The contributor is 50–59, female. The patient indicates the lesion is rough or flaky and raised or bumpy. The lesion involves the leg, arm and back of the hand. The patient considered this a rash. The lesion is associated with pain, bleeding, darkening, enlargement, itching, burning and bothersome appearance. Reported duration is more than one year. Self-reported Fitzpatrick IV; lay reviewers estimated Monk Skin Tone 3 or 4 (two reviewer pools). An image taken at a distance. Associated systemic symptoms include joint pain and fatigue — 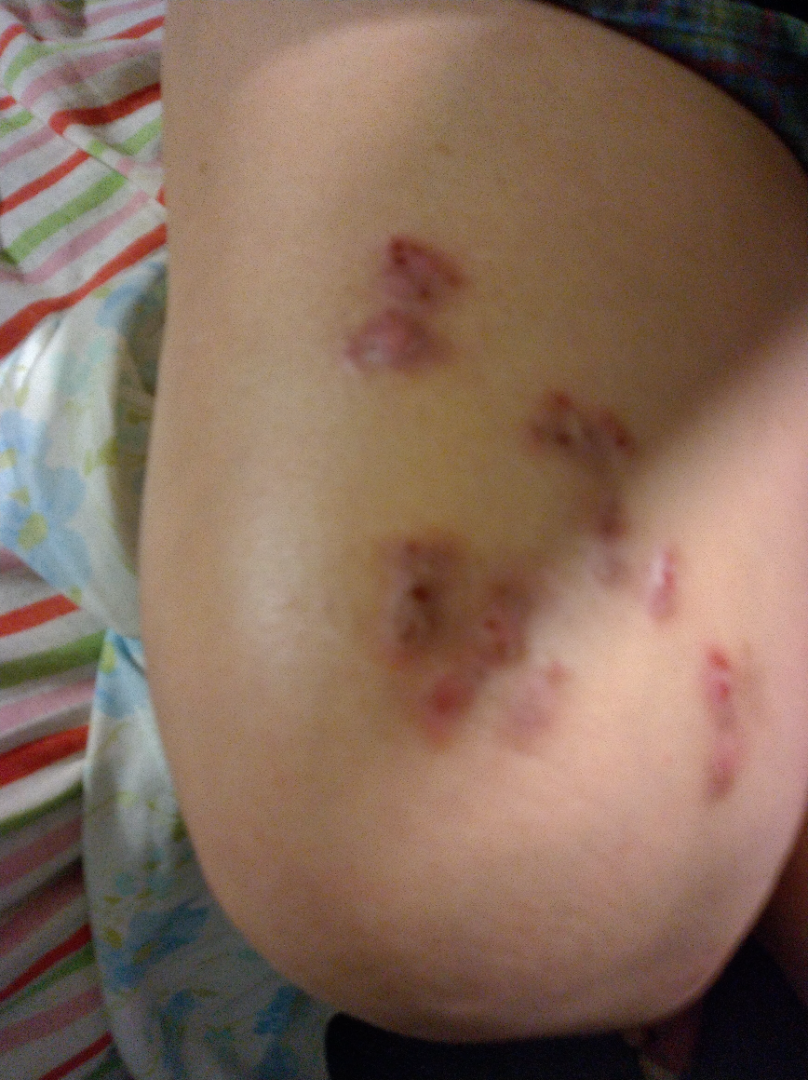Review:
The condition could not be reliably identified from the image.